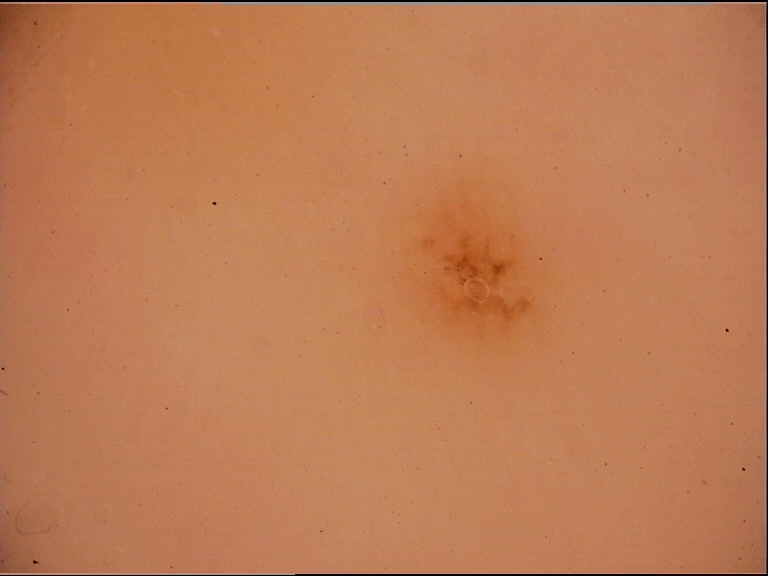A dermoscopic image of a skin lesion. The architecture is that of a banal lesion. The diagnostic label was an acral junctional nevus.